A skin lesion imaged with a dermatoscope.
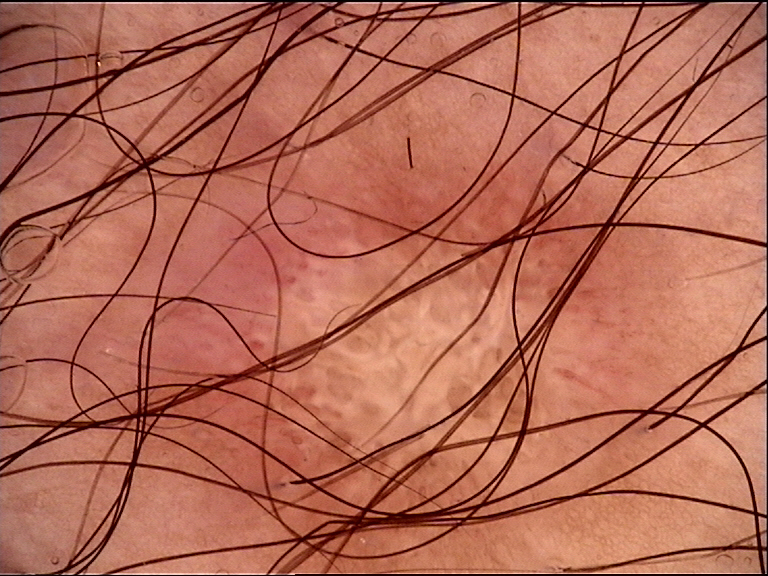lesion type: fibro-histiocytic | class: dermatofibroma (expert consensus).